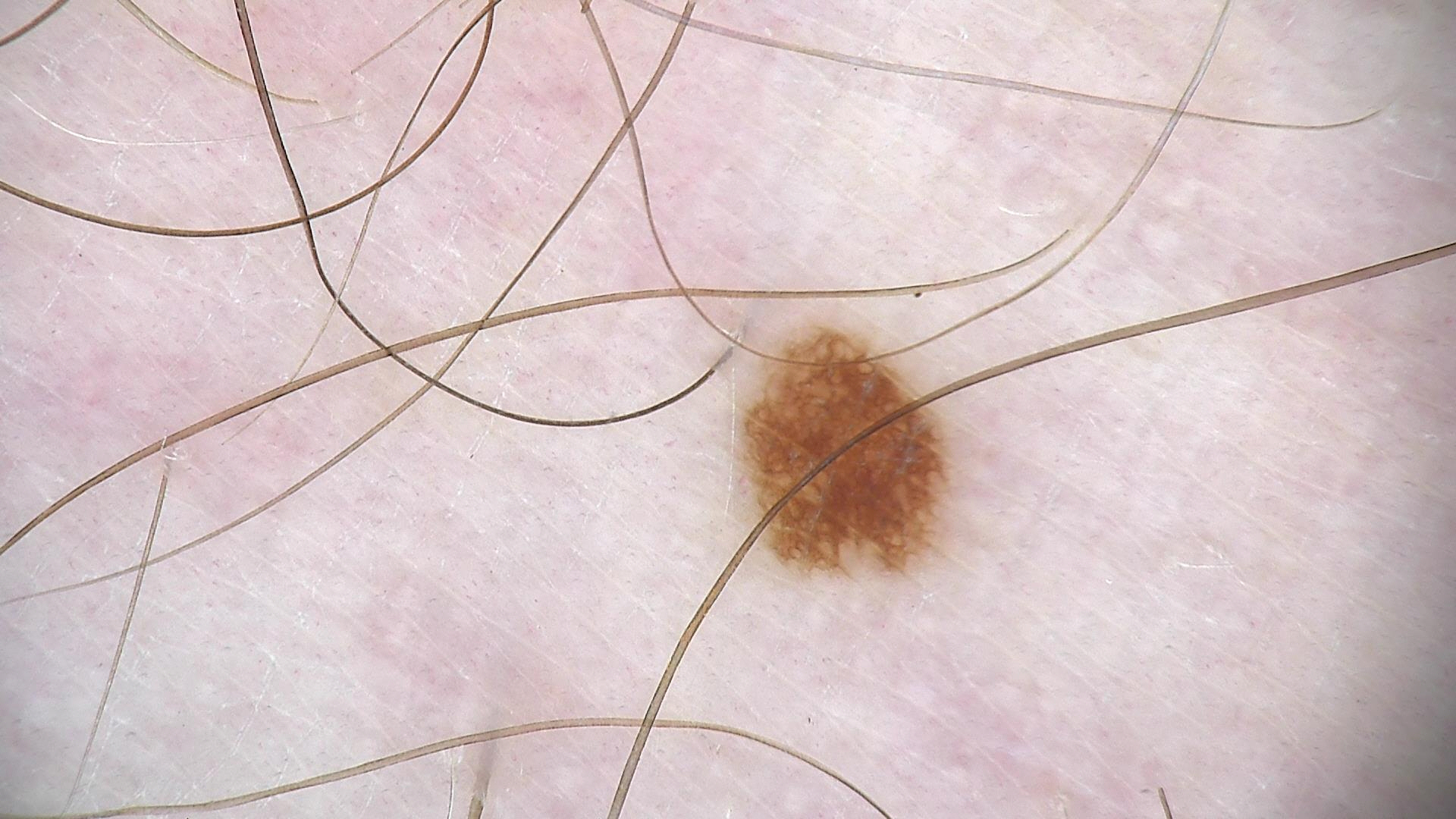class — dysplastic junctional nevus (expert consensus).